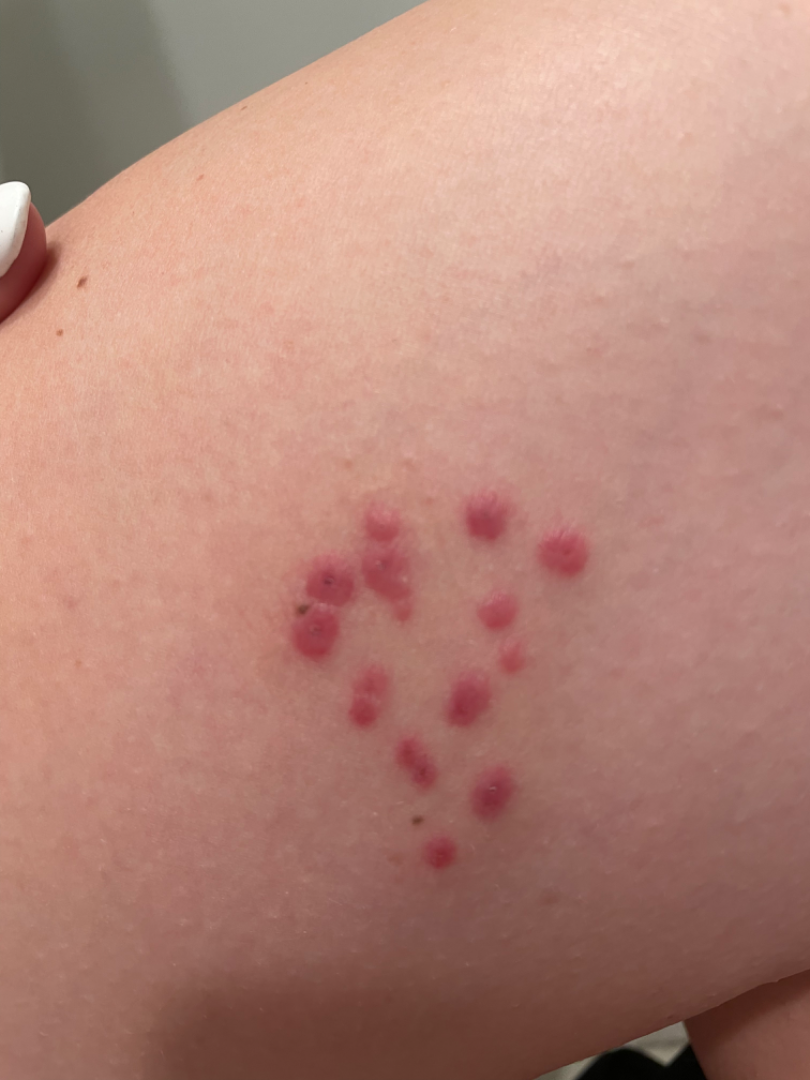| key | value |
|---|---|
| framing | at an angle |
| location | leg |
| subject | female, age 18–29 |
| clinical impression | Insect Bite (favored); Herpes Zoster (considered); Molluscum Contagiosum (unlikely); Herpes Simplex (unlikely); Sweet syndrome (unlikely) |